A close-up photograph. The leg and arm are involved:
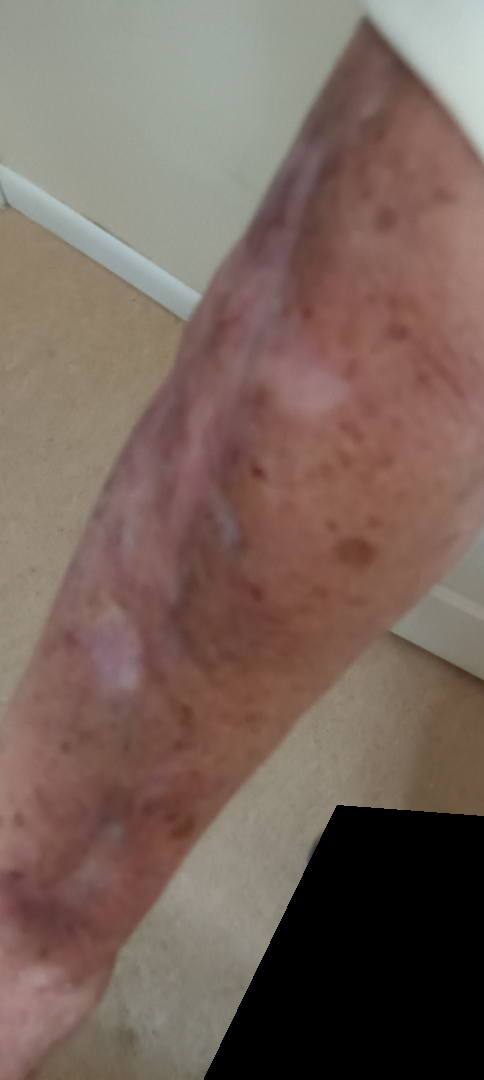Case summary:
– assessment — could not be assessed